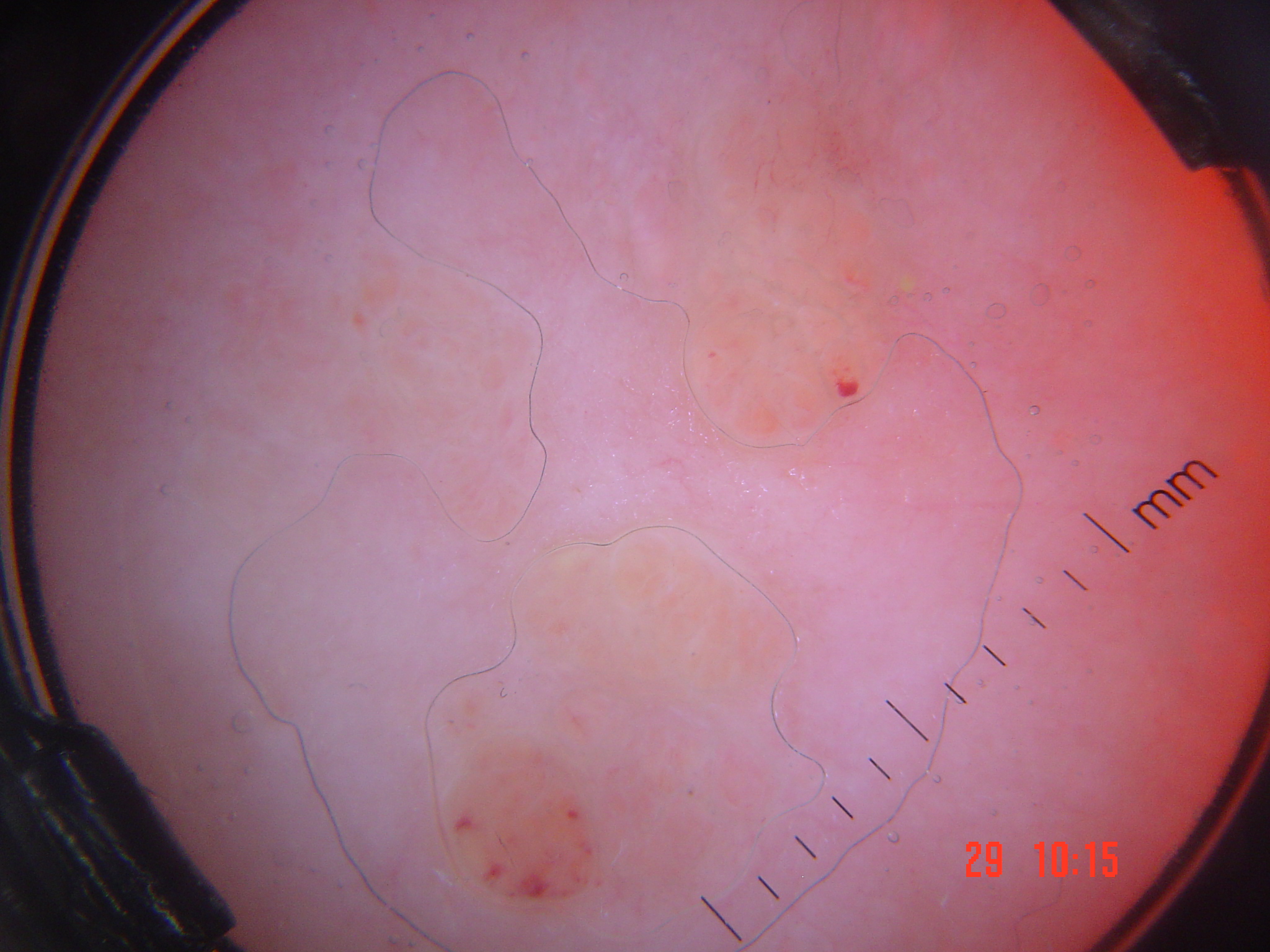image: dermoscopy
lesion_type:
  main_class: vascular
diagnosis:
  name: lymphangioma
  code: la
  malignancy: benign
  super_class: non-melanocytic
  confirmation: expert consensus